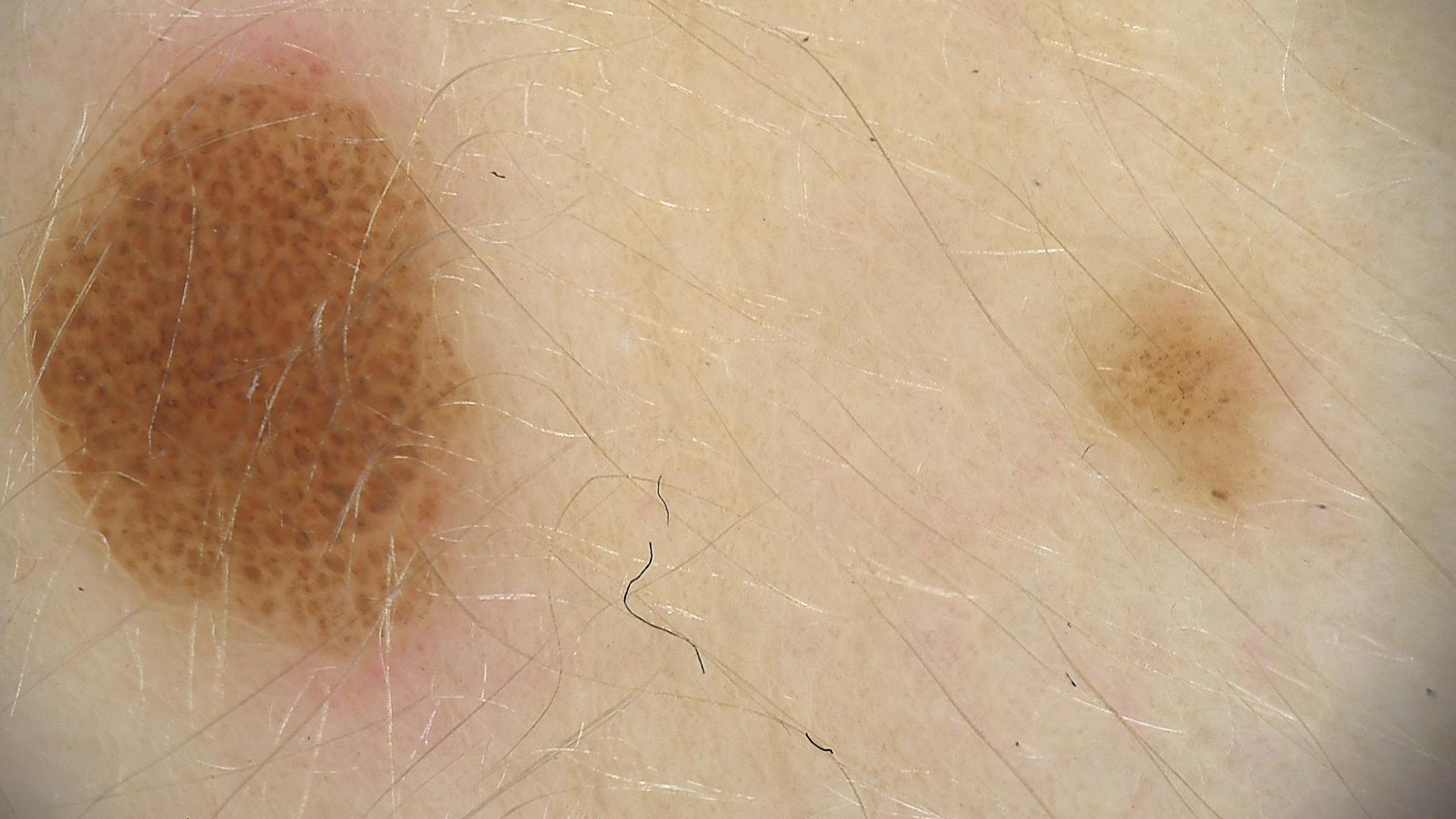Case:
* class: compound nevus (expert consensus)